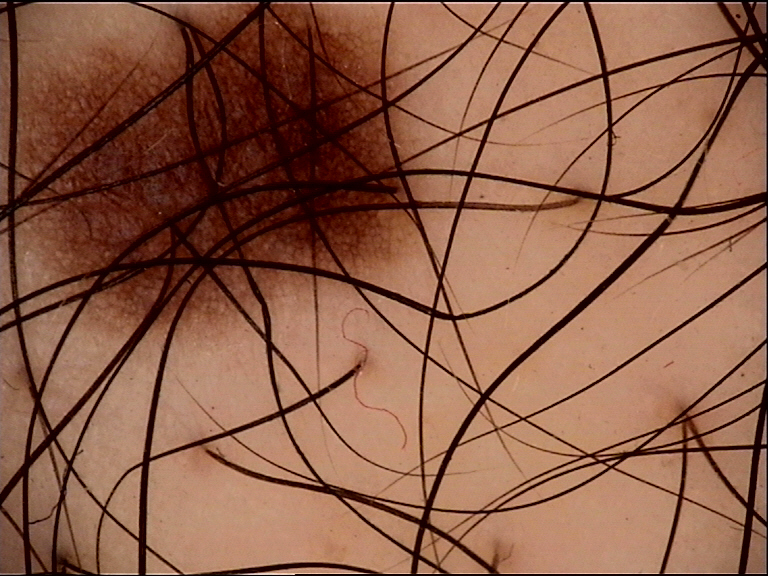<case>
  <diagnosis>
    <name>dysplastic junctional nevus</name>
    <code>jd</code>
    <malignancy>benign</malignancy>
    <super_class>melanocytic</super_class>
    <confirmation>expert consensus</confirmation>
  </diagnosis>
</case>